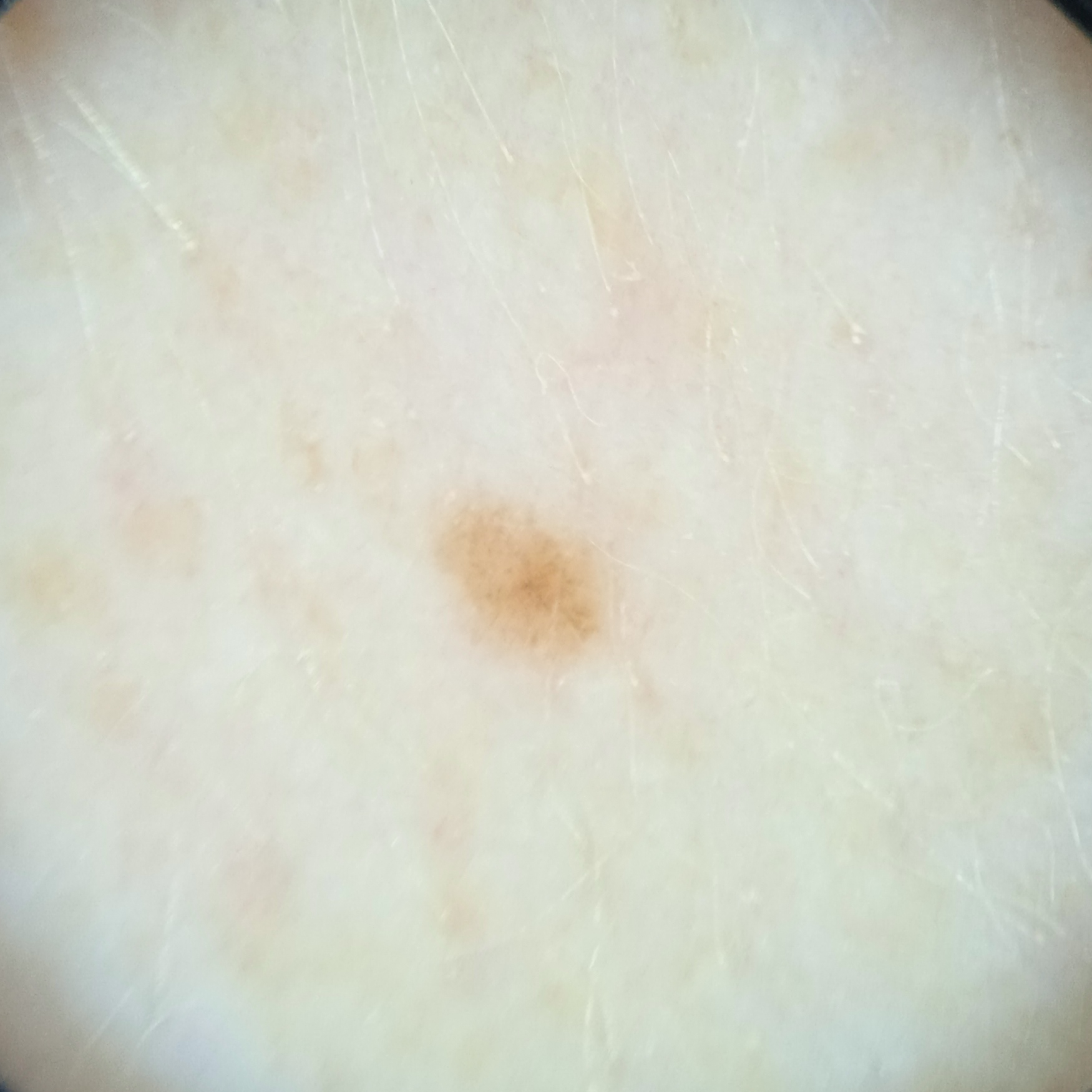The patient says their skin reddens painfully with sun exposure. A female patient 50 years of age. A dermoscopic image of a skin lesion. A moderate number of moles by the patient's own estimate. The lesion is on an arm. The lesion is about 2 mm across. Dermatologist review favored a melanocytic nevus.